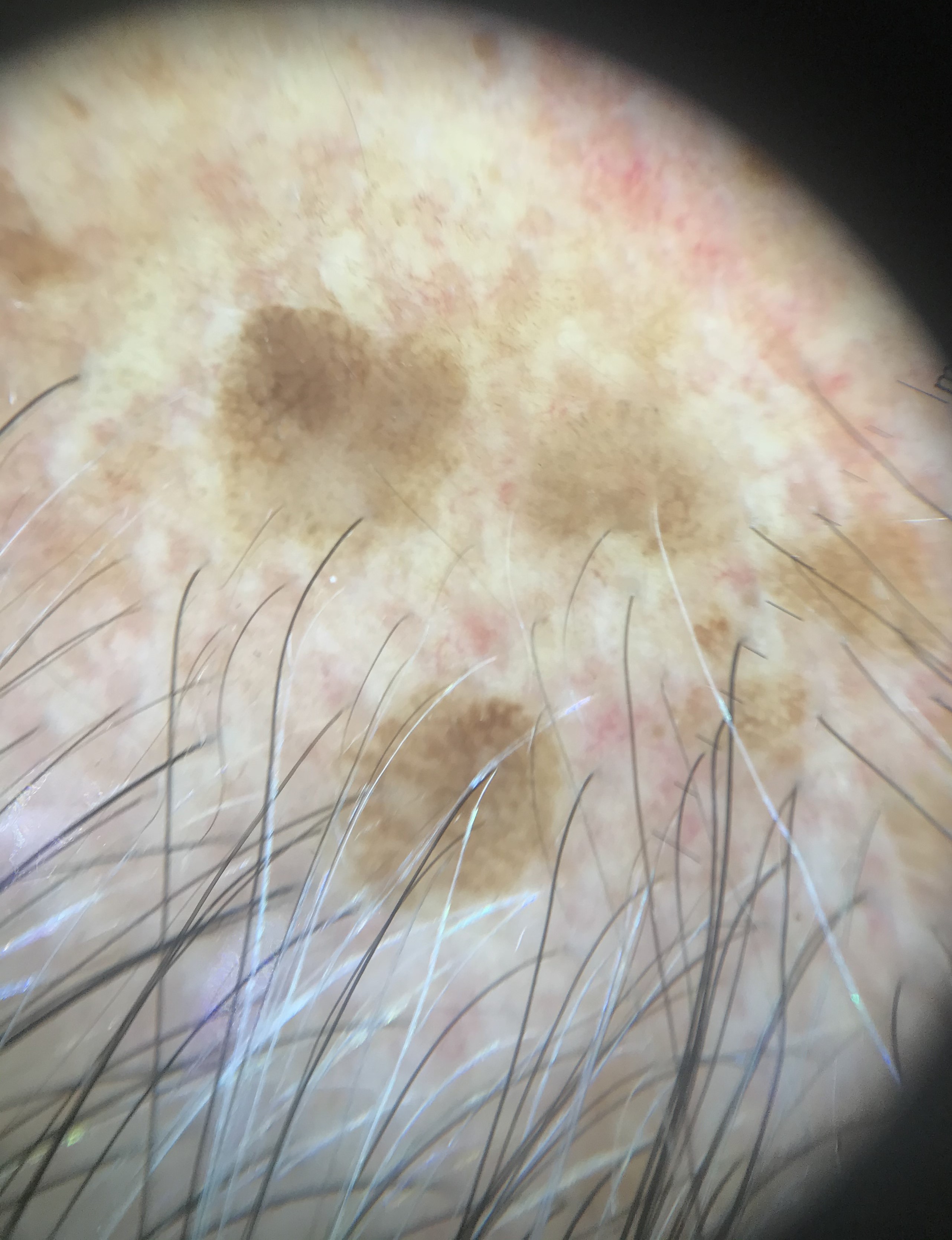  diagnosis:
    name: seborrheic keratosis
    code: sk
    malignancy: benign
    super_class: non-melanocytic
    confirmation: expert consensus